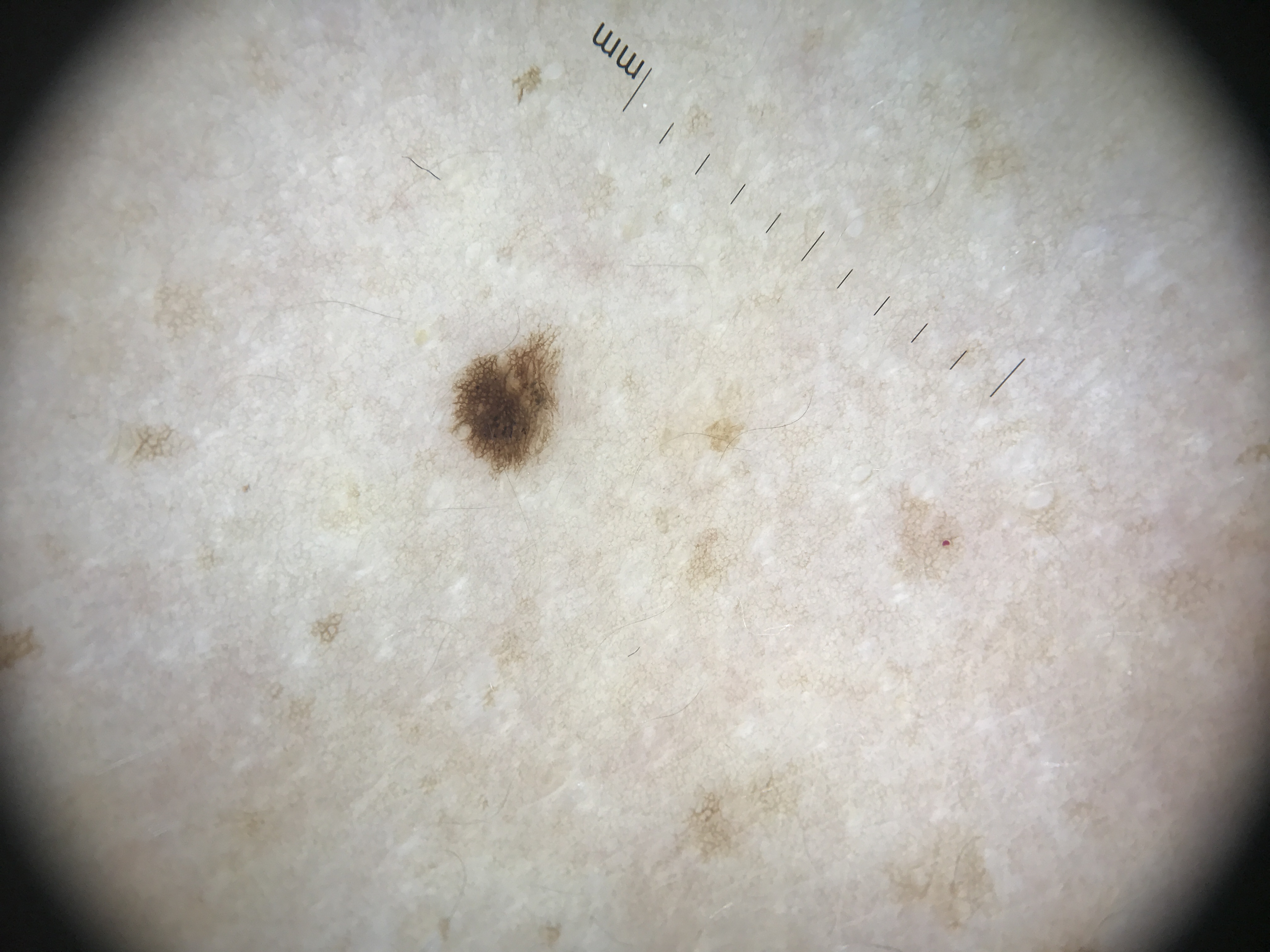Labeled as a benign lesion — a dysplastic junctional nevus.